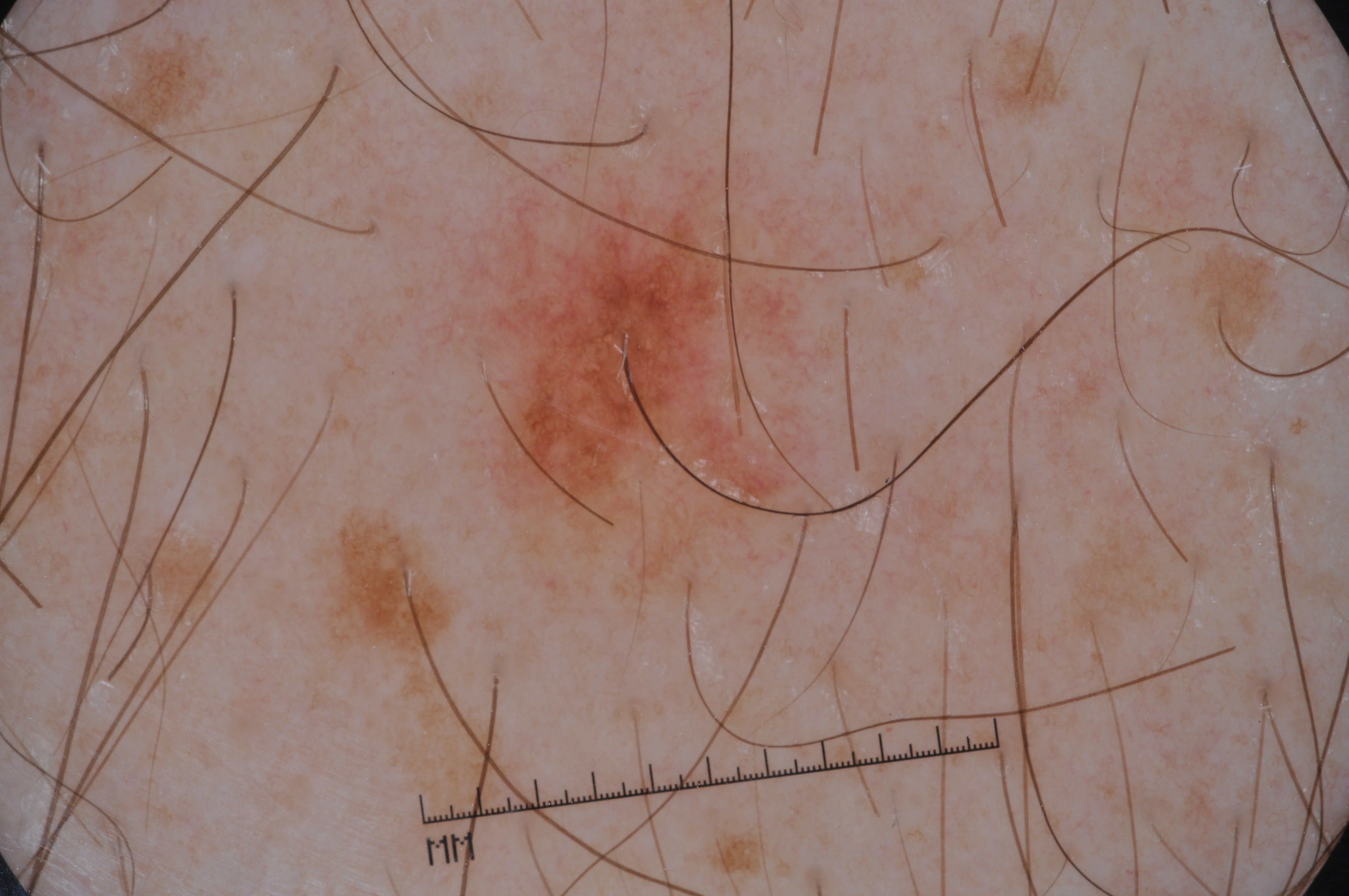image type: dermatoscopic image of a skin lesion
dermoscopic findings: pigment network
bounding box: <box>485, 196, 790, 525</box>
diagnosis: a melanocytic nevus